The photo was captured at a distance. The affected area is the leg:
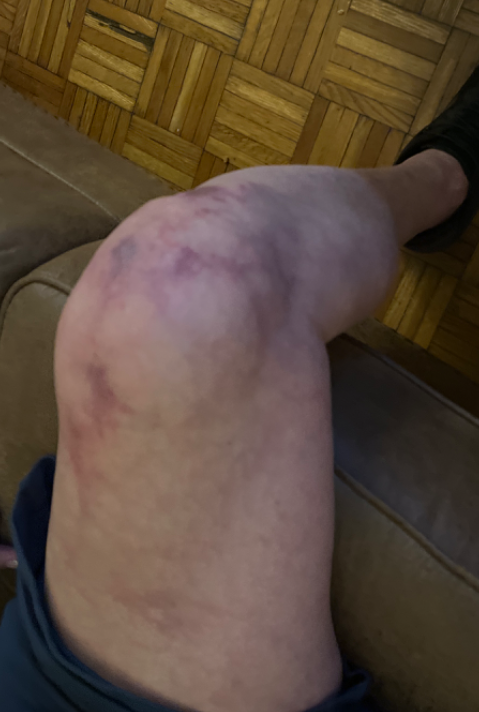<dermatology_case>
<assessment>not assessable</assessment>
</dermatology_case>